Dermoscopy of a skin lesion. The patient is FST II — 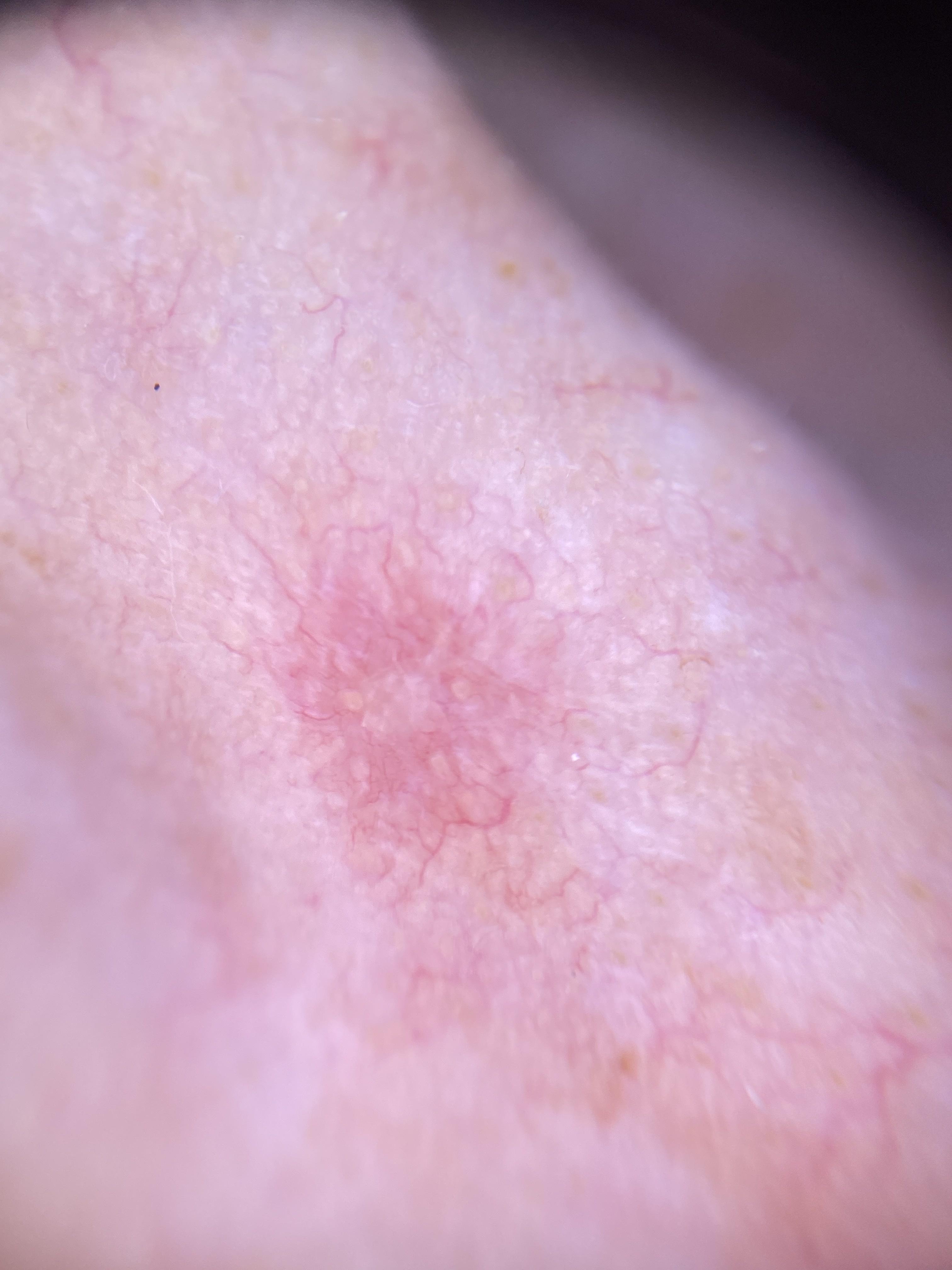The lesion is on the head or neck. Histopathologically confirmed as a squamous cell carcinoma.